A dermatoscopic image of a skin lesion: 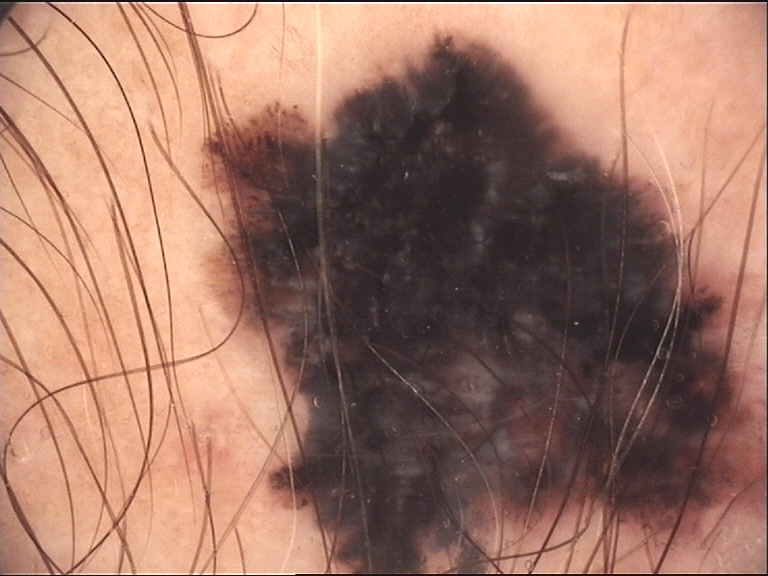class: melanoma (biopsy-proven).